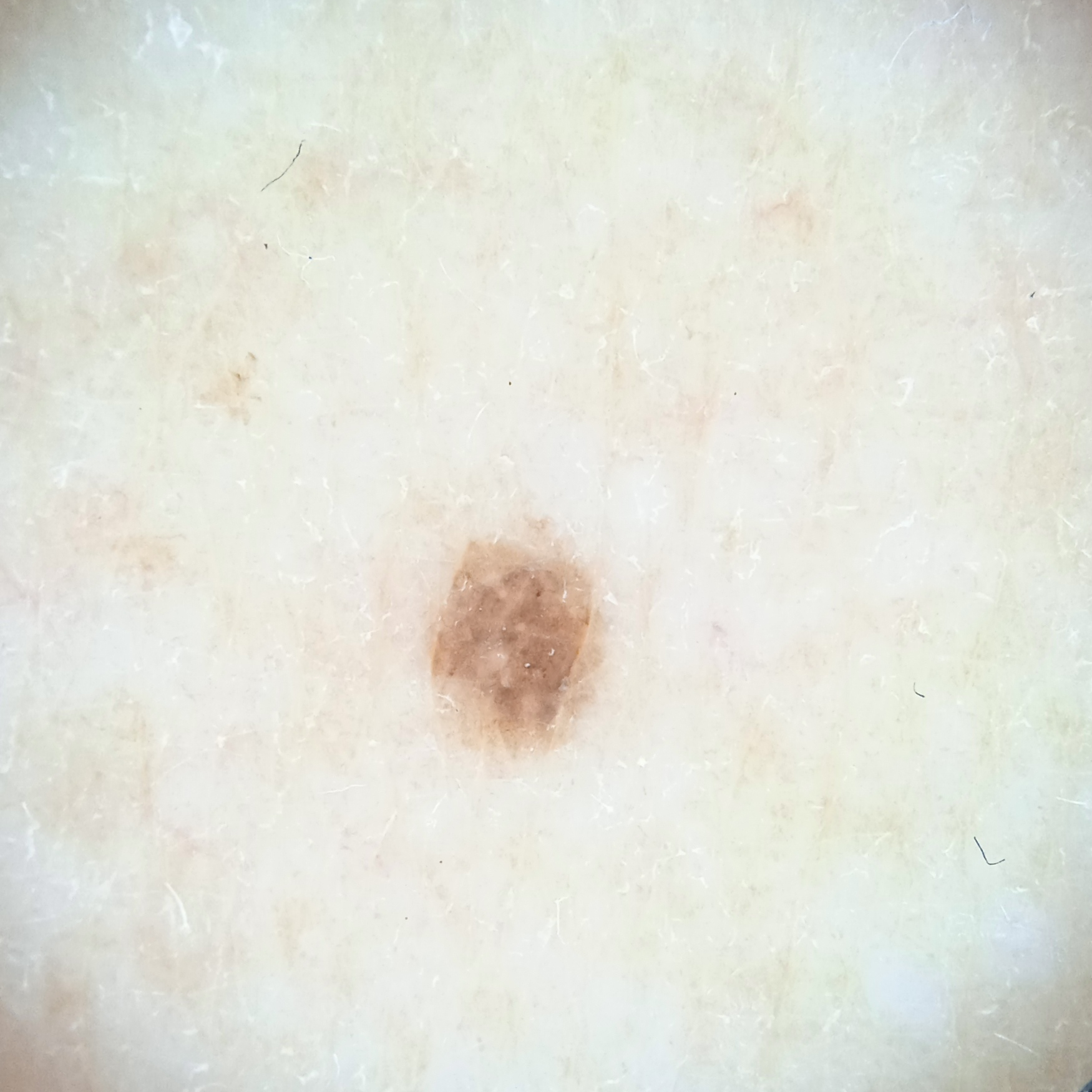Conclusion: The dermatologists' assessment was a melanocytic nevus.